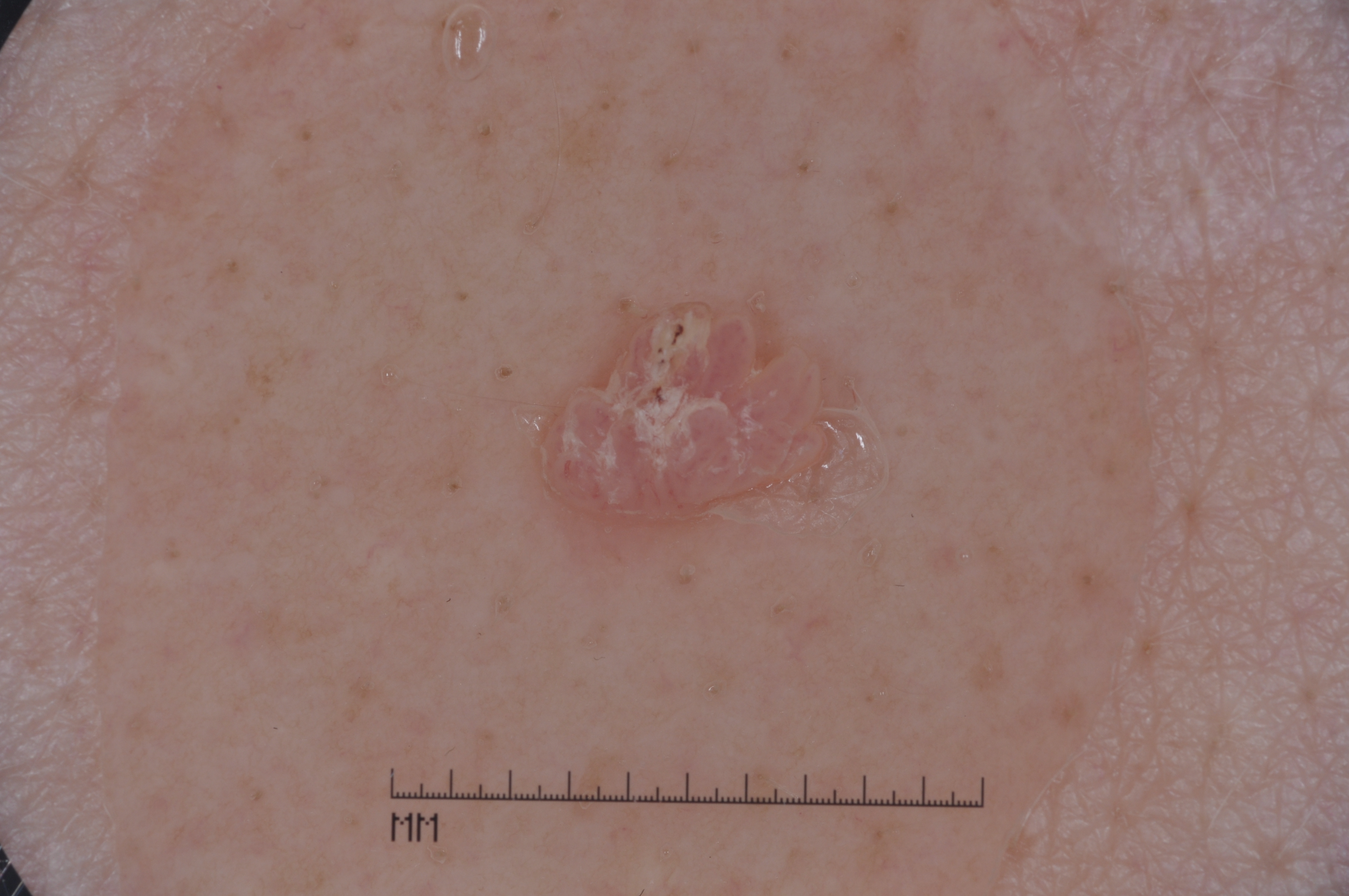A male patient aged 48-52. A dermatoscopic image of a skin lesion. As (left, top, right, bottom), the lesion's extent is 401, 266, 875, 595. Dermoscopy demonstrates no streaks, pigment network, negative network, or milia-like cysts. A mid-sized lesion within the field. The diagnostic assessment was a seborrheic keratosis.